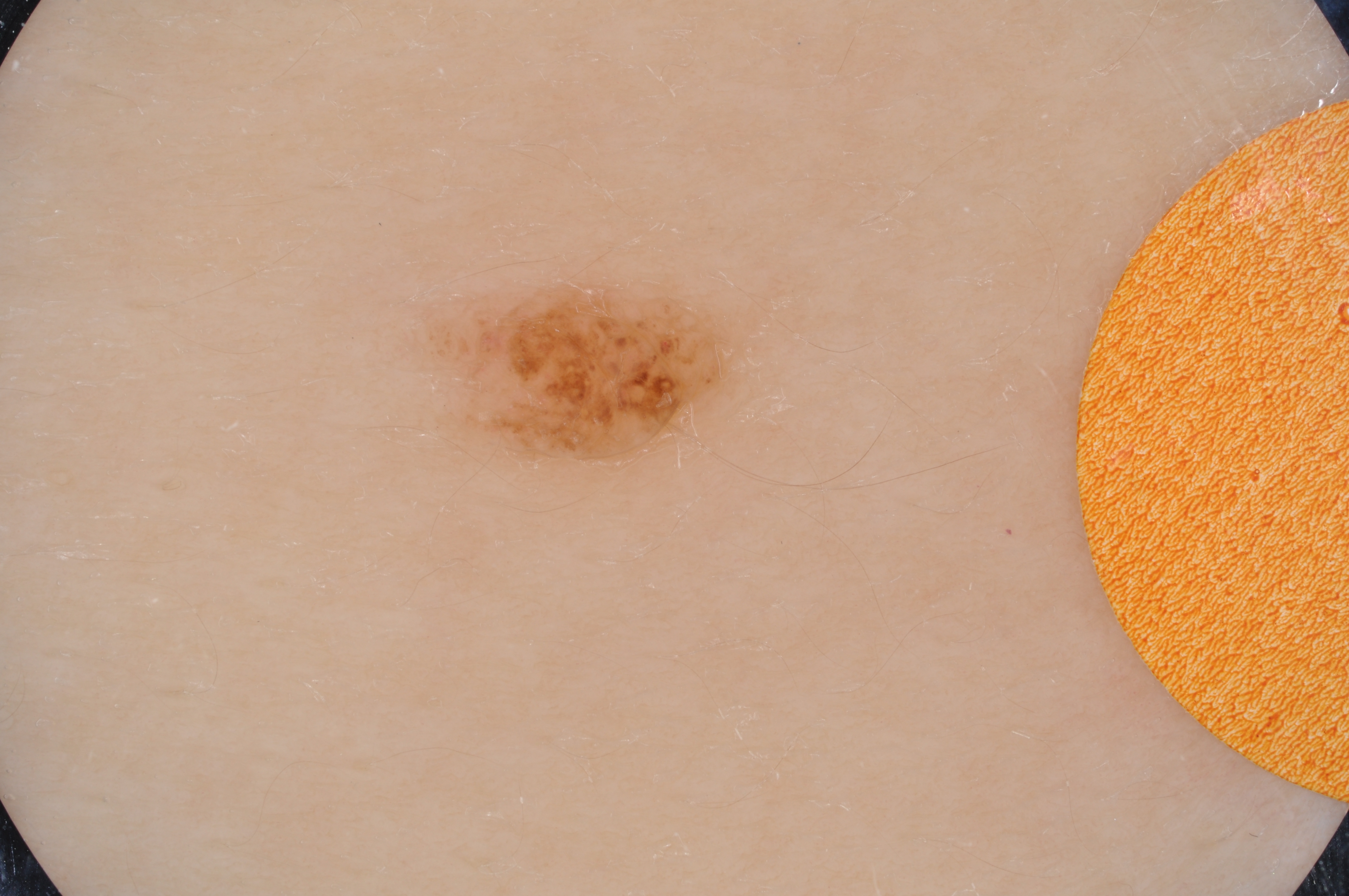| key | value |
|---|---|
| modality | dermoscopic image |
| subject | female, aged around 15 |
| lesion location | 422, 271, 757, 483 |
| dermoscopic findings | pigment network and globules; absent: negative network, milia-like cysts, and streaks |
| impression | a melanocytic nevus, a benign skin lesion |